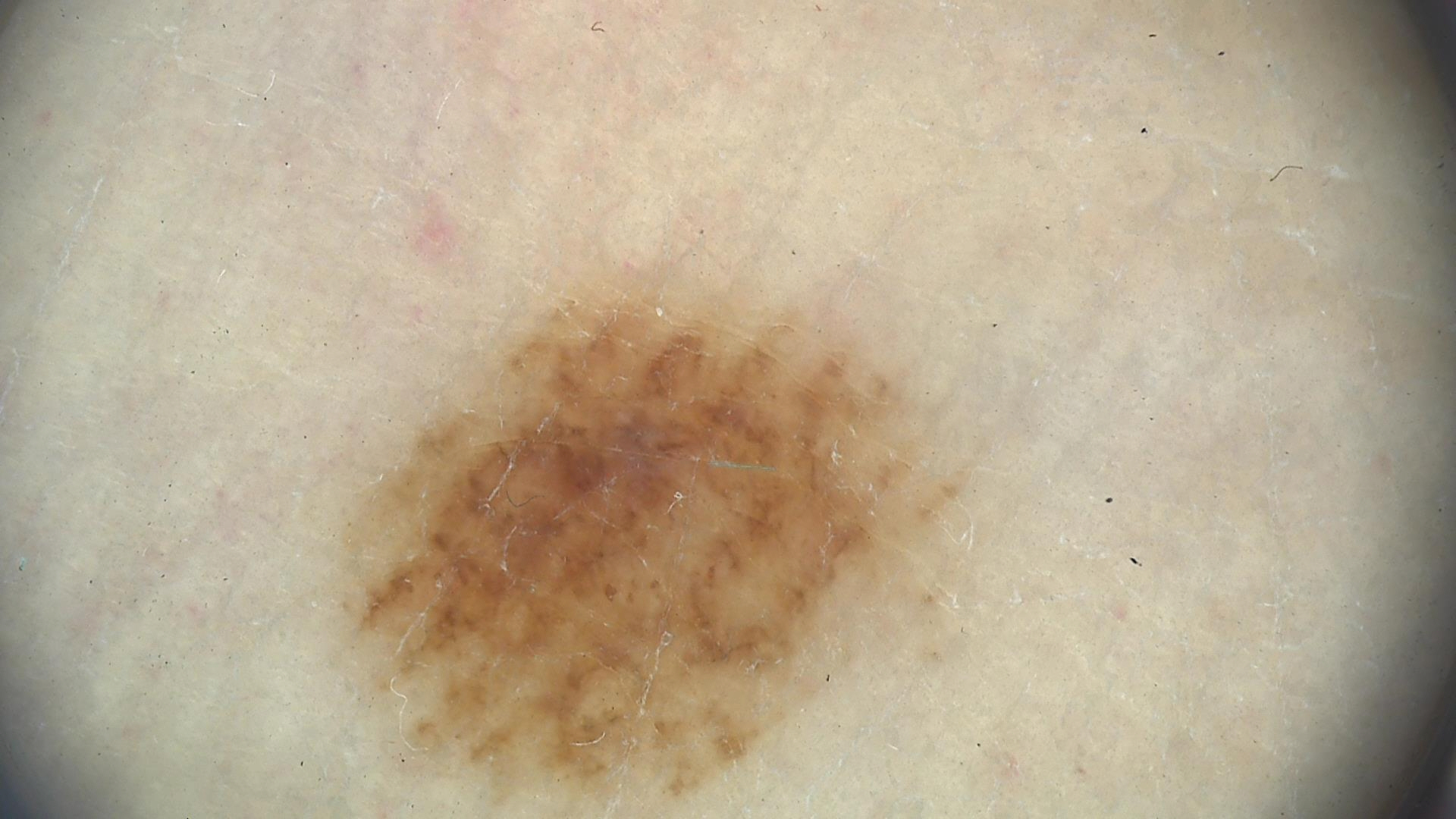diagnosis:
  name: acral compound nevus
  code: acb
  malignancy: benign
  super_class: melanocytic
  confirmation: expert consensus